Recorded as FST II. A male patient in their 80s.
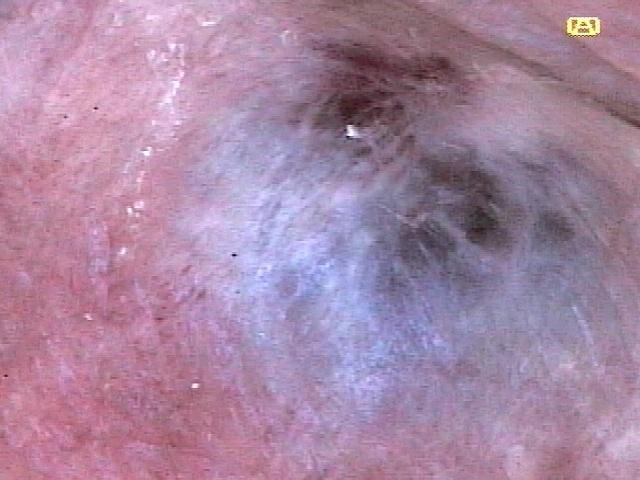anatomic site — the head or neck; diagnosis — Basal cell carcinoma (biopsy-proven).